Located on the leg; the contributor is male; a close-up photograph.
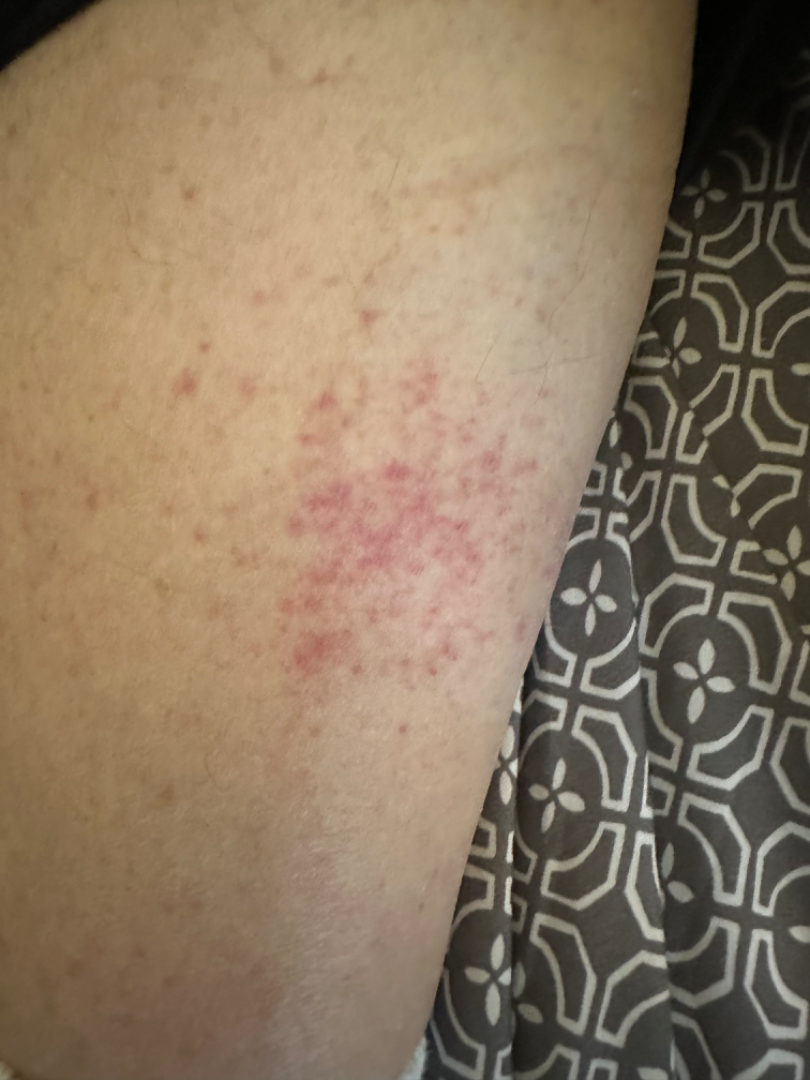differential diagnosis: Acute dermatitis, NOS and Irritant Contact Dermatitis were considered with similar weight.